Acquired for a research image collection, with no referral diagnosis · the patient says their skin reddens with sun exposure · a clinical photograph of a skin lesion · a female subject 67 years of age — 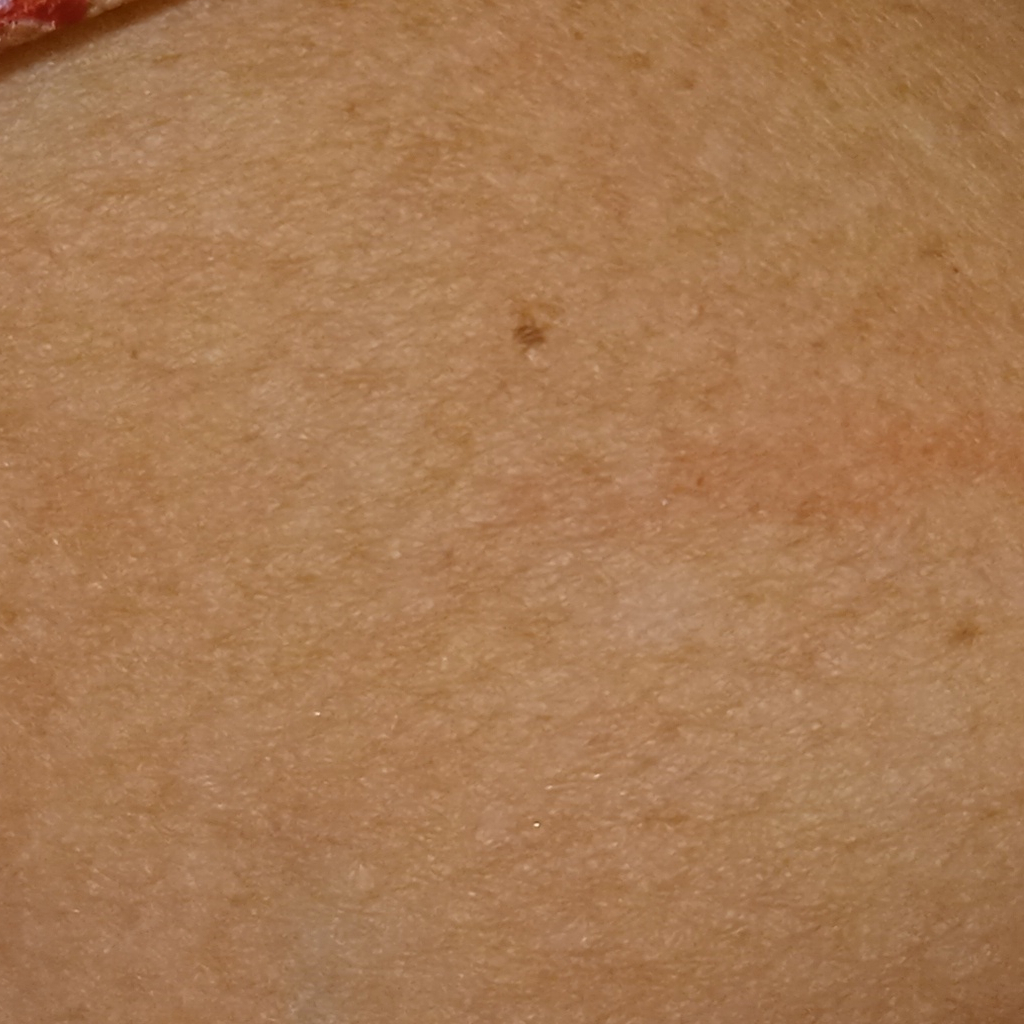Q: Lesion size?
A: 1.3 mm
Q: What was the diagnosis?
A: melanocytic nevus (dermatologist consensus)